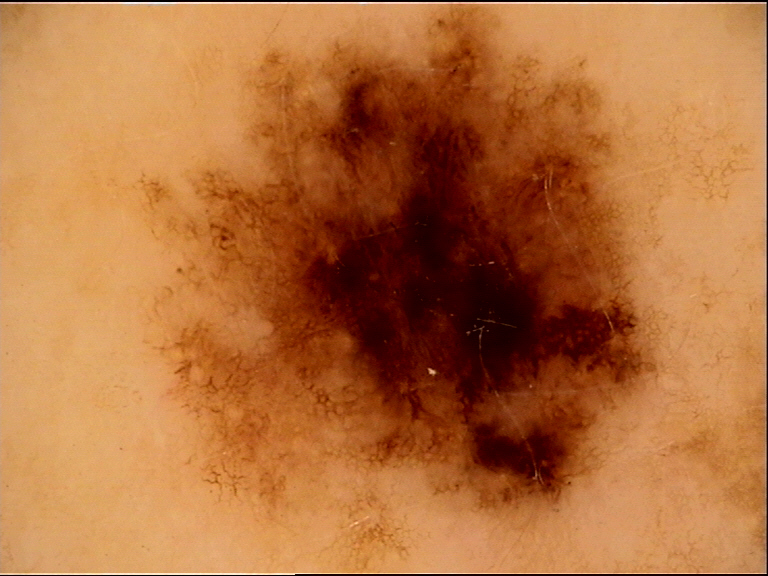A skin lesion imaged with a dermatoscope.
The biopsy diagnosis was a melanoma.